The patient is a female aged 40–49. The photograph was taken at an angle. Located on the arm — 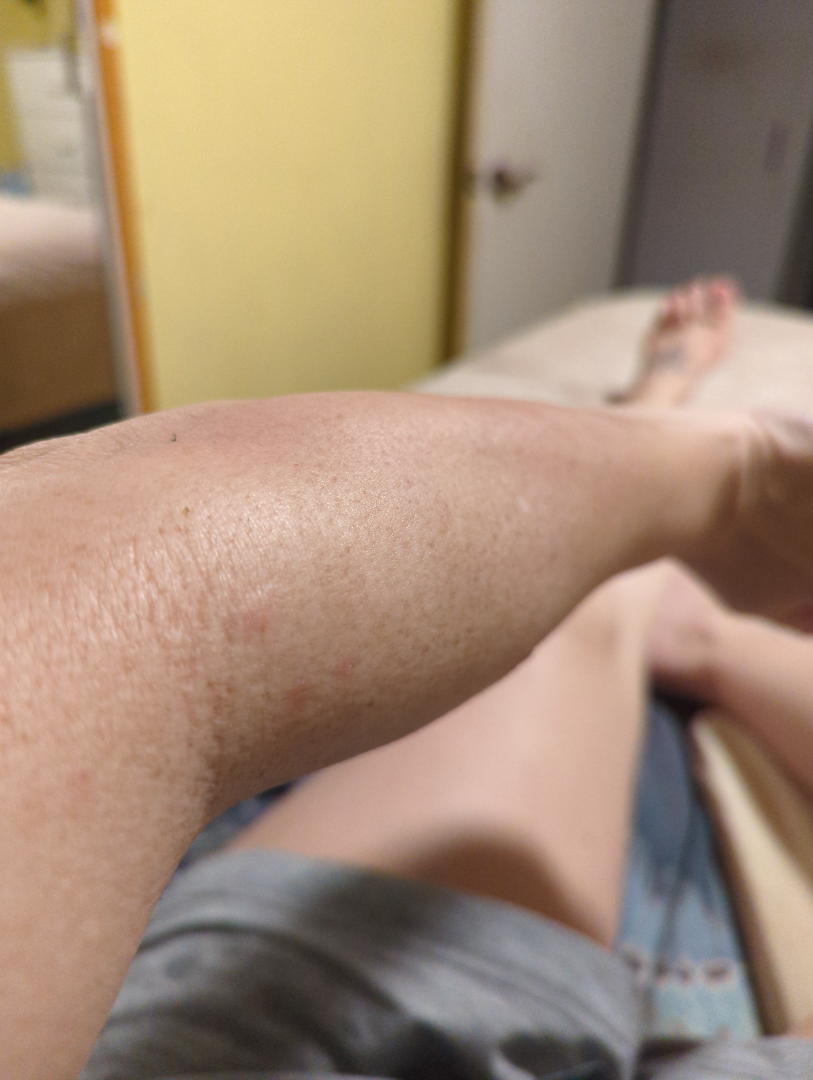Notes:
• assessment · indeterminate from the photograph
• present for · more than one year
• patient's own categorization · a rash
• associated systemic symptoms · fatigue and joint pain
• lesion symptoms · pain, burning and itching